This image was taken at an angle: 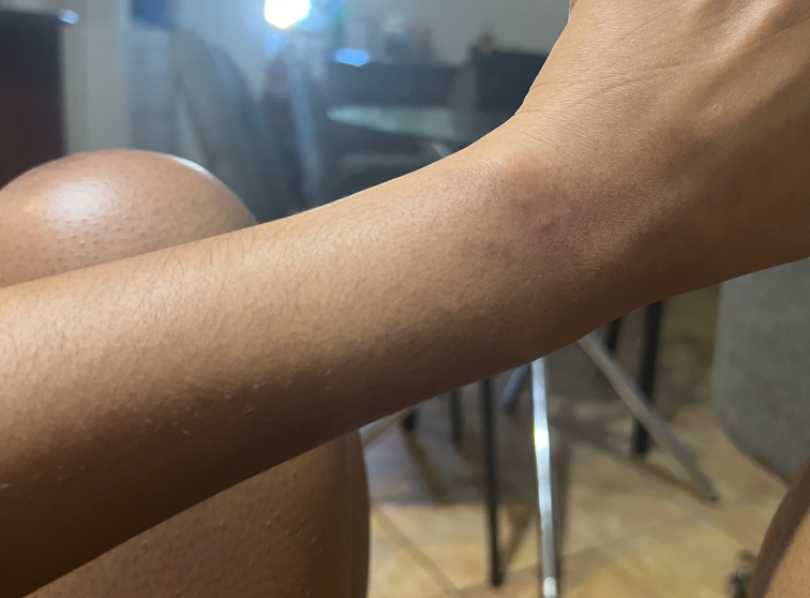Q: What conditions are considered?
A: Allergic Contact Dermatitis (weight 0.67); Irritant Contact Dermatitis (weight 0.33)